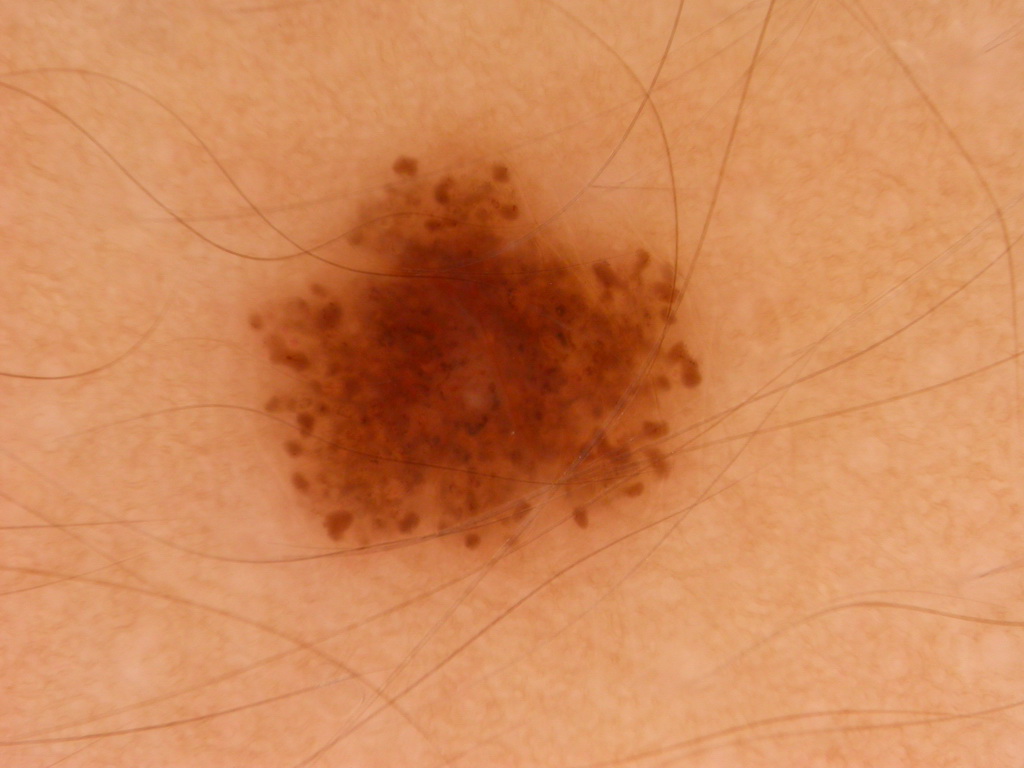• imaging — dermoscopic image
• lesion bbox — bbox=[247, 151, 697, 551]
• assessment — a melanocytic nevus